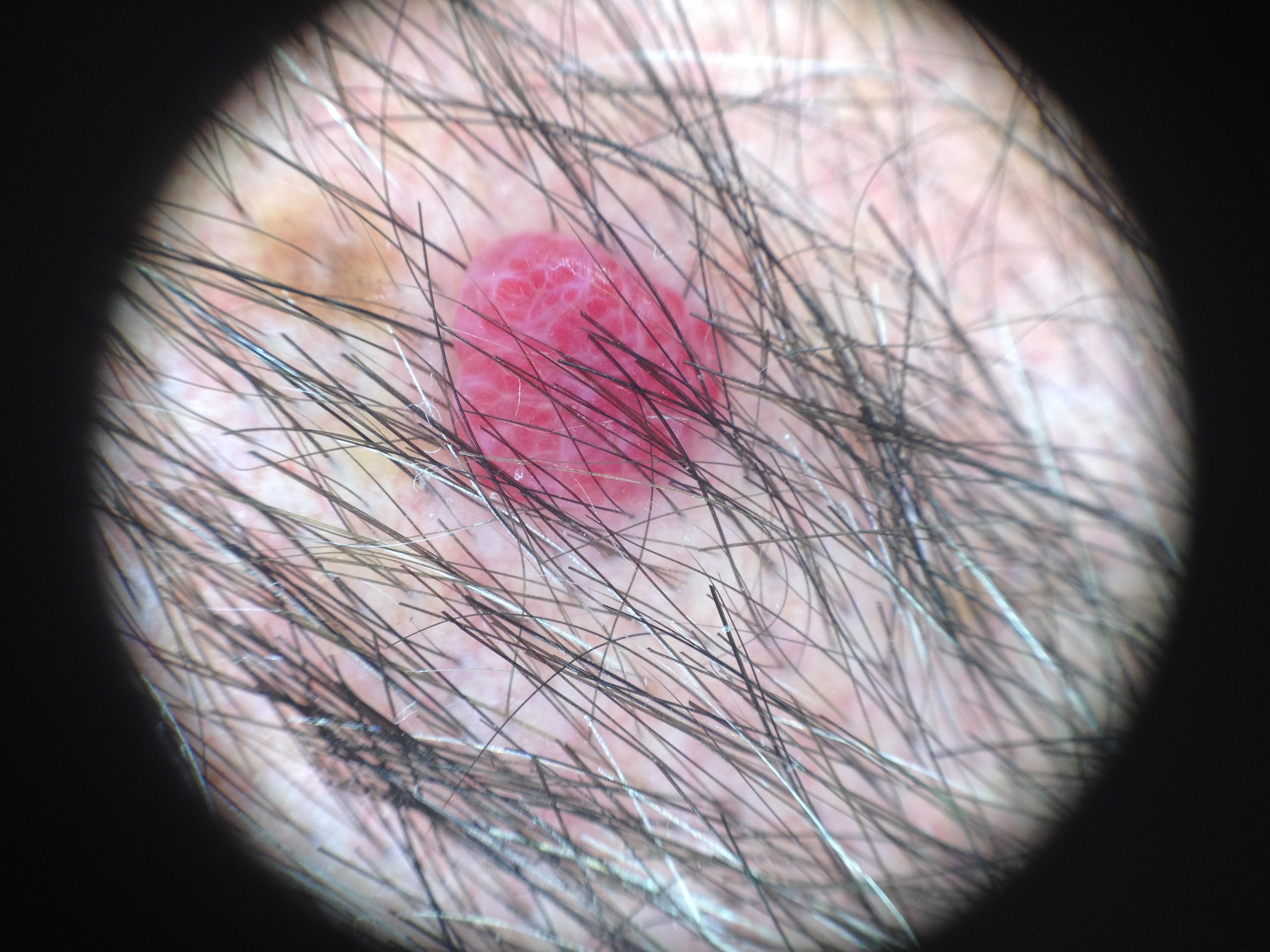A skin lesion imaged with contact-polarized dermoscopy. FST II. The chart records a previous melanoma but no first-degree relative with melanoma. A male patient about 55 years old. The lesion is located on the head or neck. The clinical assessment was a vascular lesion.